The lesion involves the leg. The photograph was taken at a distance. The contributor is 50–59, female:
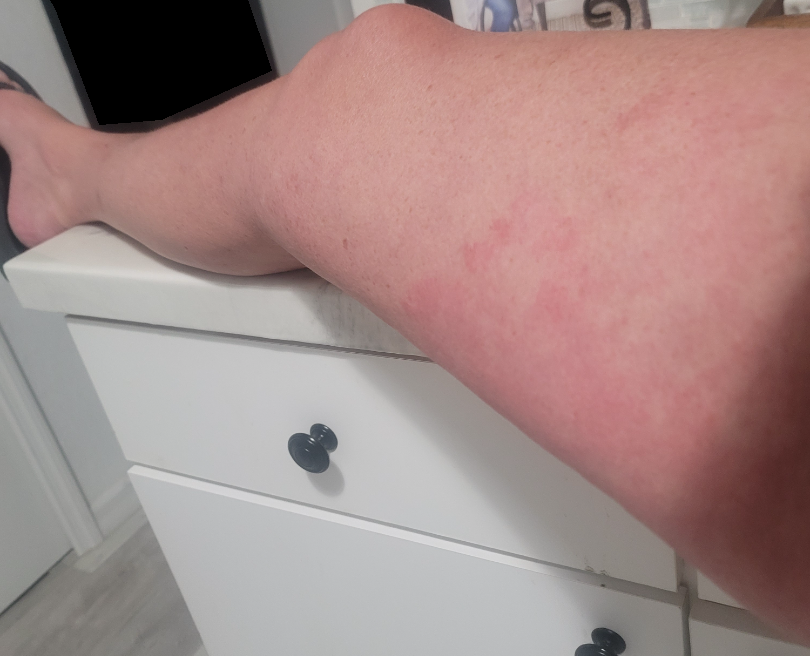– differential — Hypersensitivity, Allergic Contact Dermatitis and Erythema migrans were considered with similar weight